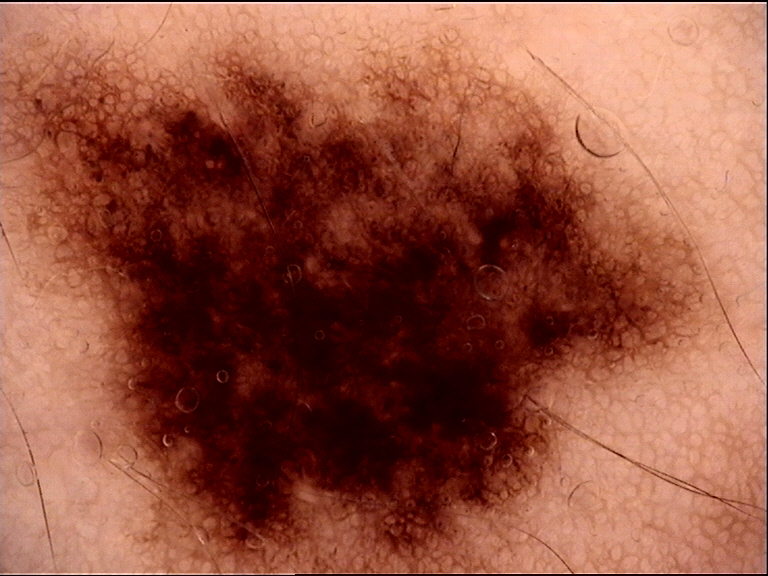A skin lesion imaged with a dermatoscope. Labeled as a dysplastic junctional nevus.